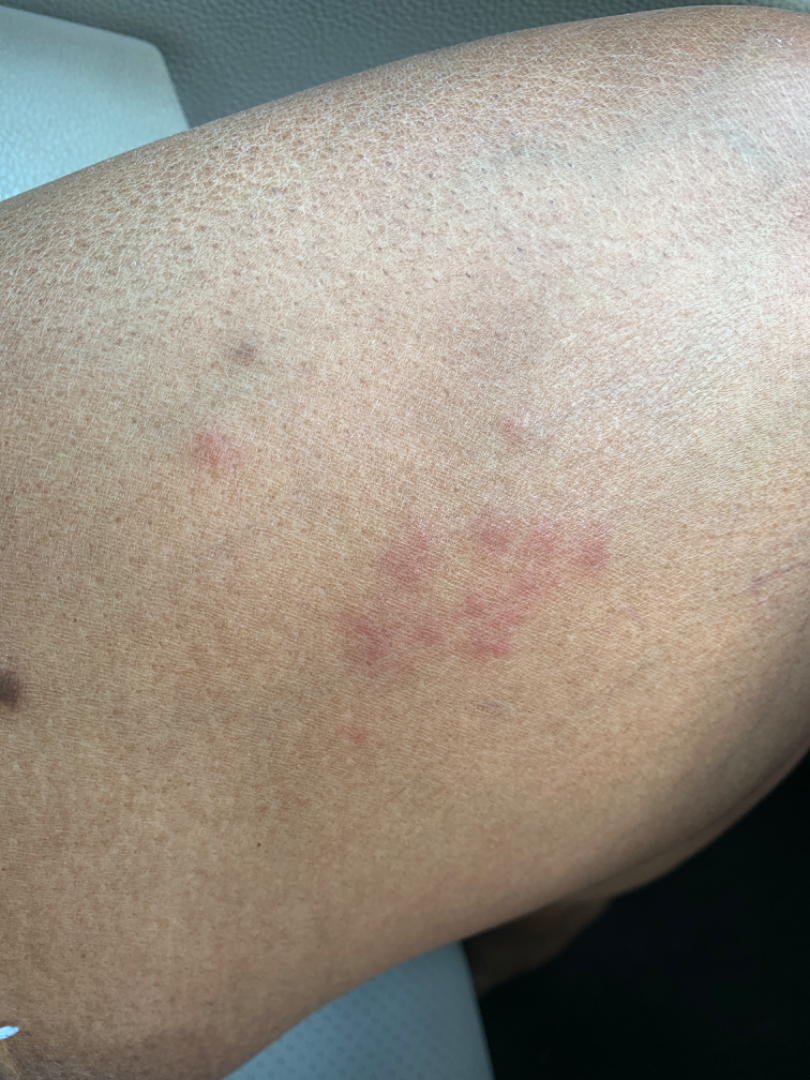Assessment: The case was difficult to assess from the available photograph. Clinical context: The lesion involves the leg. The photograph is a close-up of the affected area.